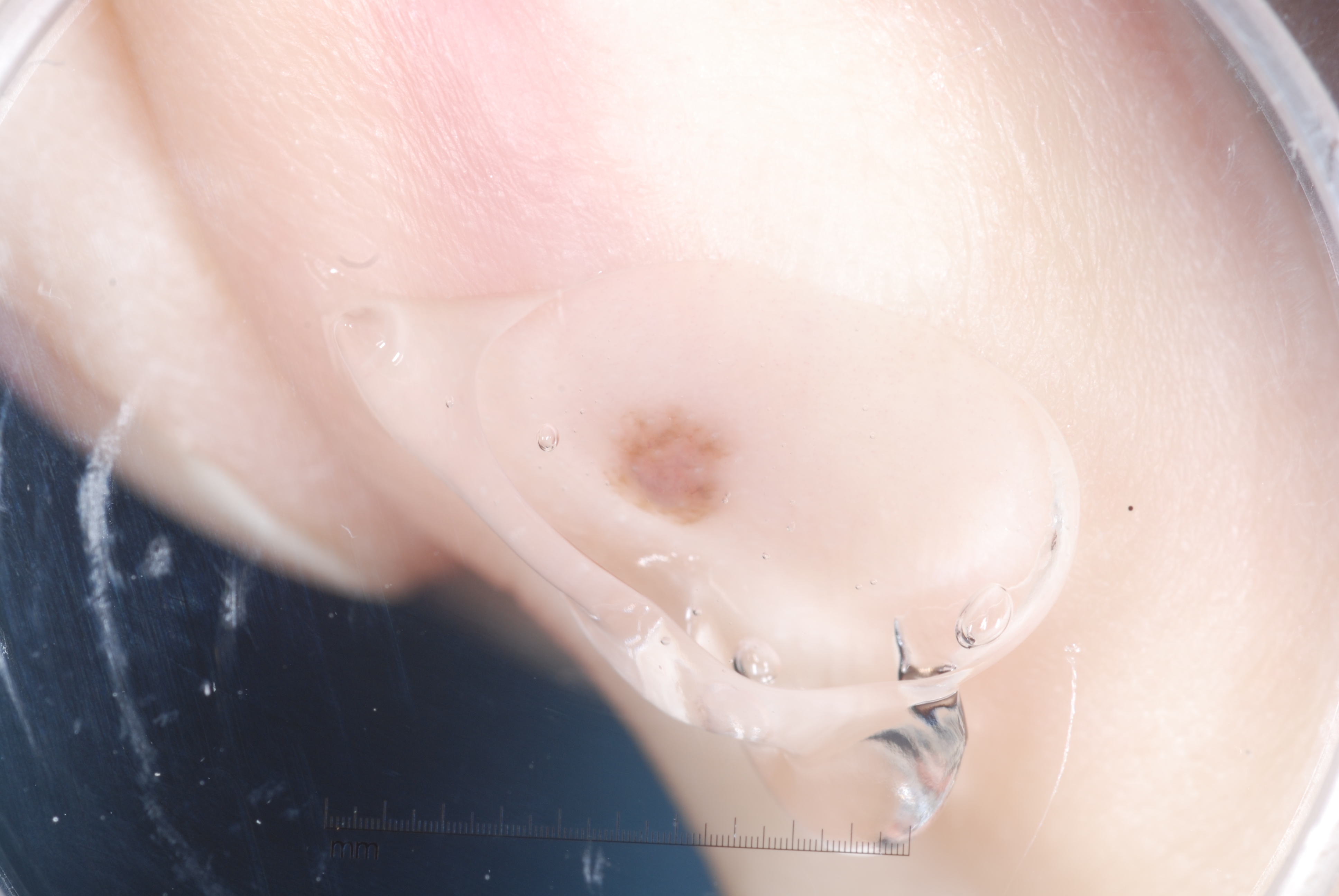| feature | finding |
|---|---|
| imaging | dermoscopy of a skin lesion |
| absent dermoscopic findings | milia-like cysts, negative network, streaks, and pigment network |
| bounding box | (601, 399, 749, 526) |
| diagnostic label | a melanocytic nevus |